The photograph is a close-up of the affected area, the subject is a female aged 40–49, the lesion involves the arm — 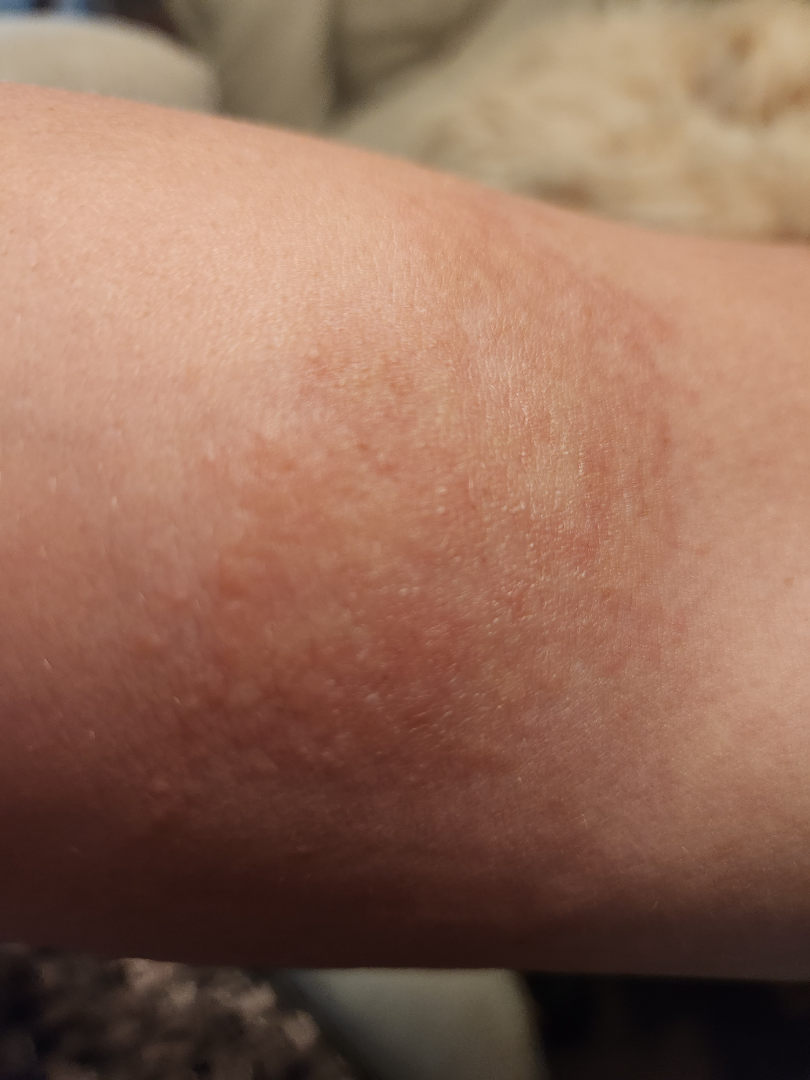Findings:
– diagnostic considerations: the differential, in no particular order, includes Photodermatitis and Acute and chronic dermatitis